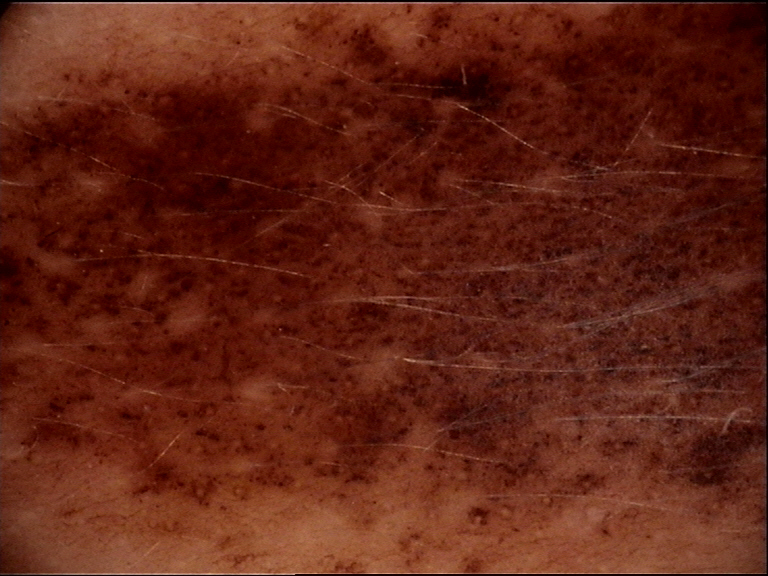- imaging: dermatoscopy
- classification: banal
- diagnostic label: congenital compound nevus (expert consensus)